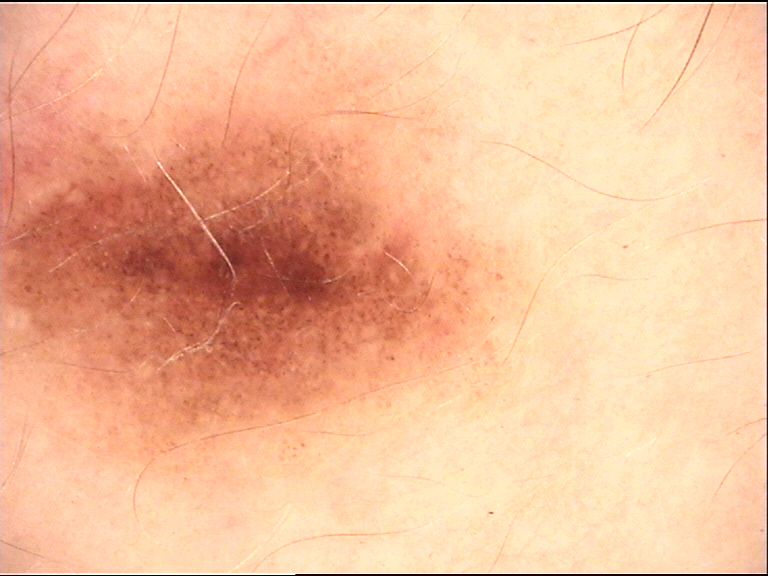Consistent with a dysplastic junctional nevus.